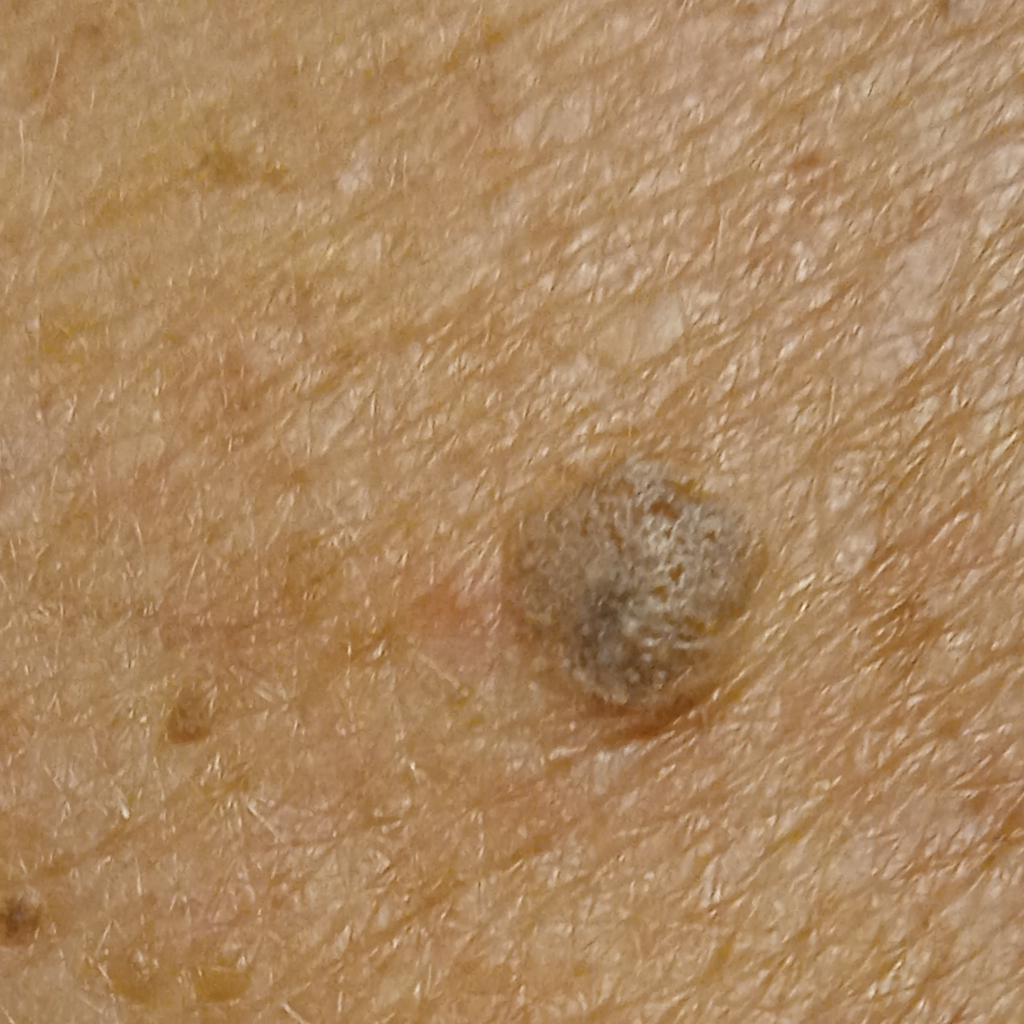The patient says their skin tans without first burning. A female subject age 78. The lesion measures approximately 7.3 mm. The diagnostic impression was a seborrheic keratosis.